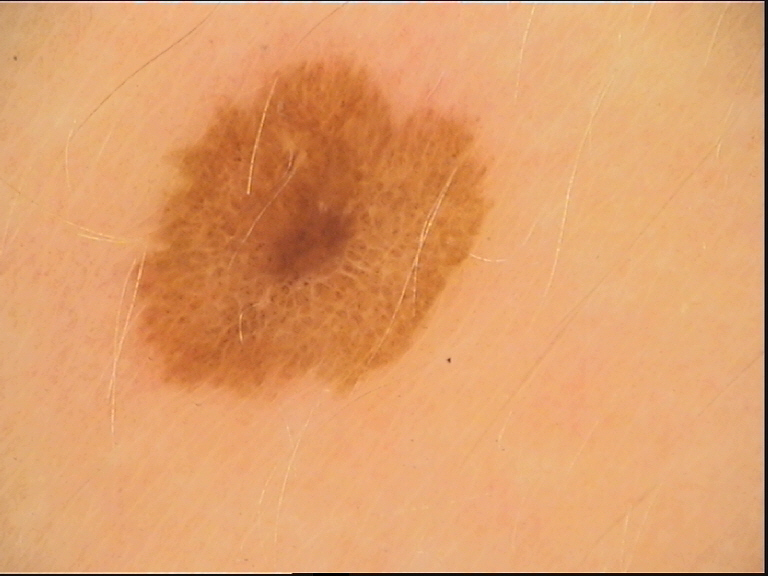image: dermatoscopy, label: dysplastic compound nevus (expert consensus).